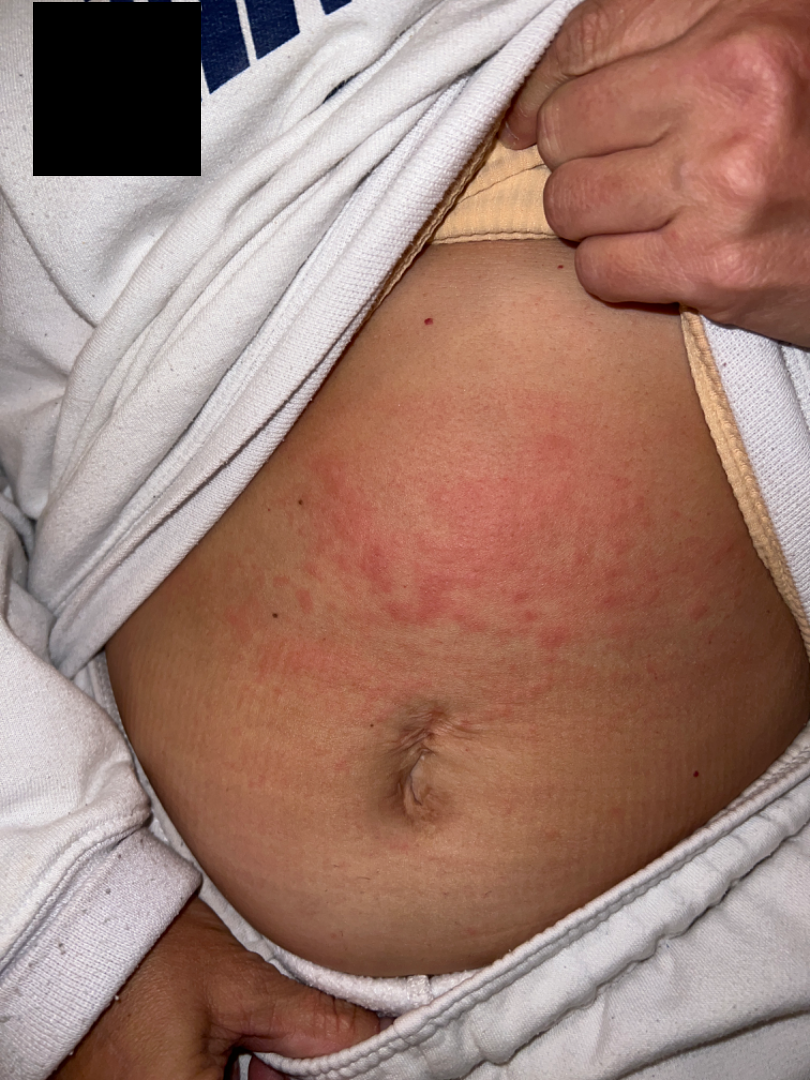Q: What conditions are considered?
A: the differential is split between Eczema and Allergic Contact Dermatitis